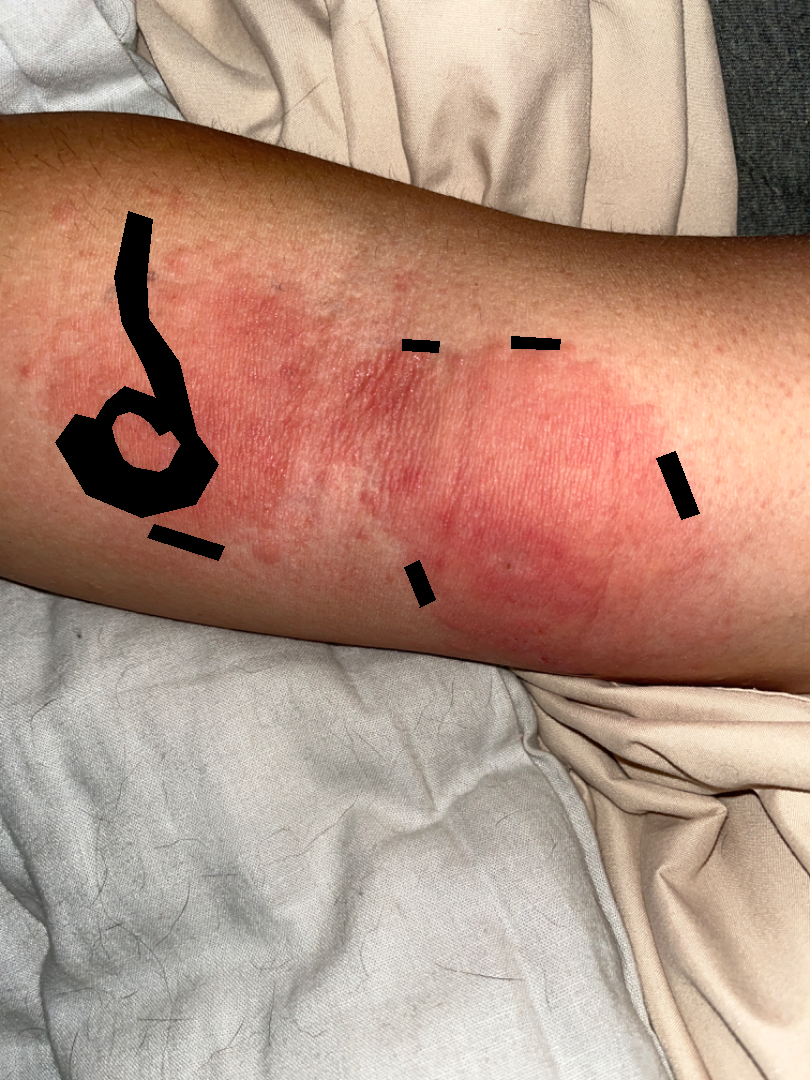framing: at an angle
skin tone: Fitzpatrick II; lay reviewers estimated MST 1 (US pool) or 2 (India pool)
subject: male, age 18–29
location: arm and head or neck
symptoms: burning and itching
texture: raised or bumpy
impression: Allergic Contact Dermatitis (weight 0.54); Urticaria (weight 0.23); Insect Bite (weight 0.23)